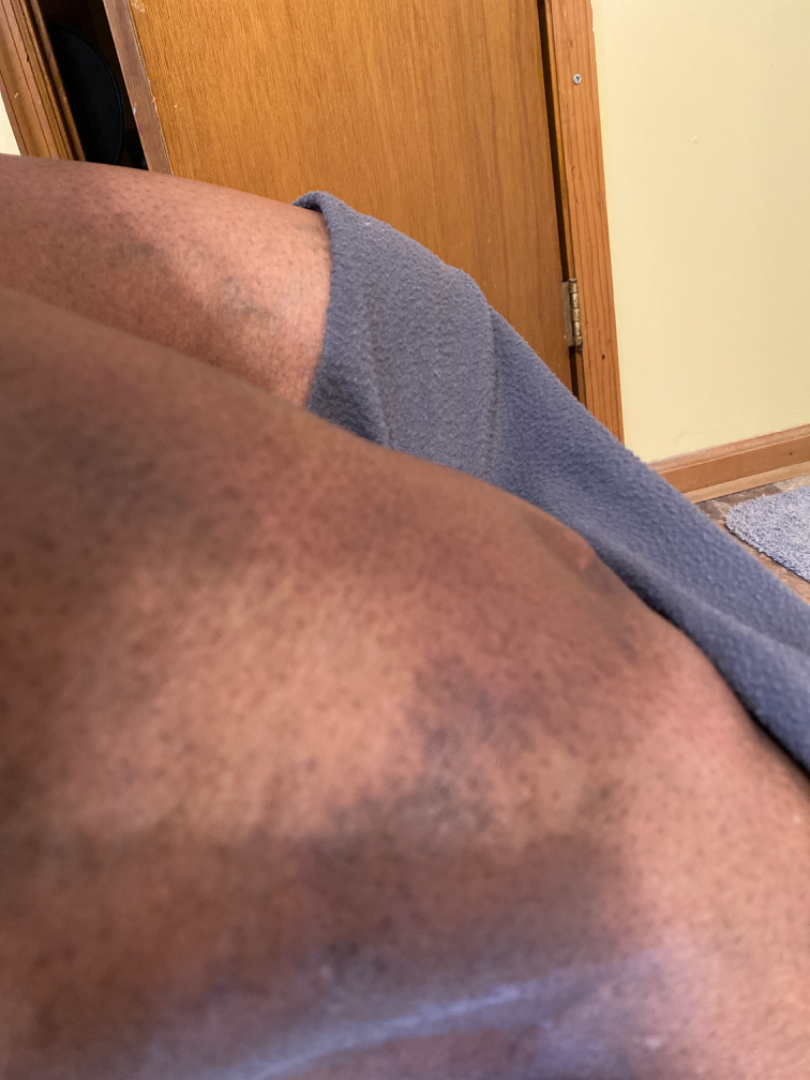The condition could not be reliably identified from the image. The patient reports the lesion is raised or bumpy. The patient reports the condition has been present for three to twelve months. The patient reported no systemic symptoms. Reported lesion symptoms include itching and burning. Close-up view. Female patient, age 50–59. Self-categorized by the patient as a hair problem. The lesion involves the leg.